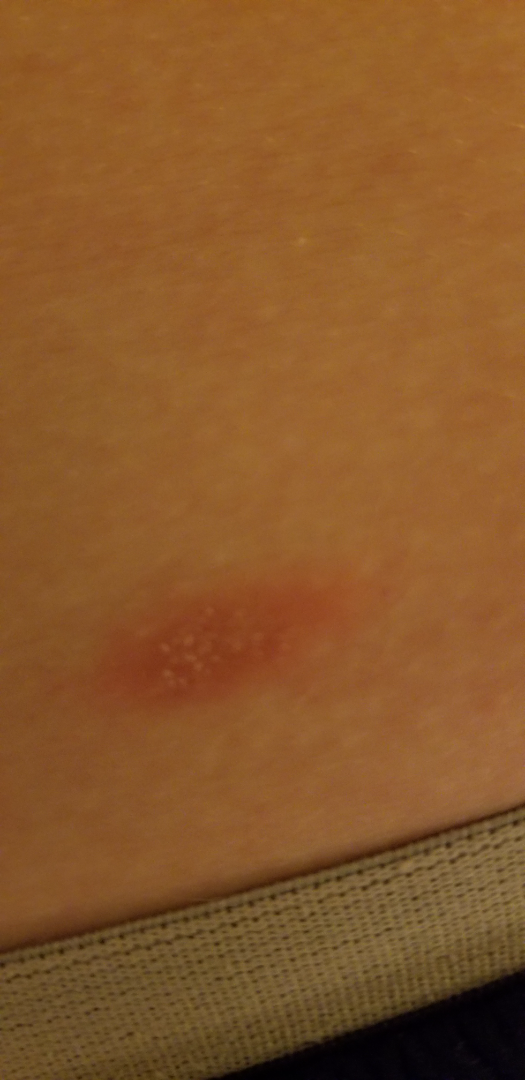Findings:
* assessment — indeterminate